A patient in their early teens · a clinical photograph of a skin lesion: 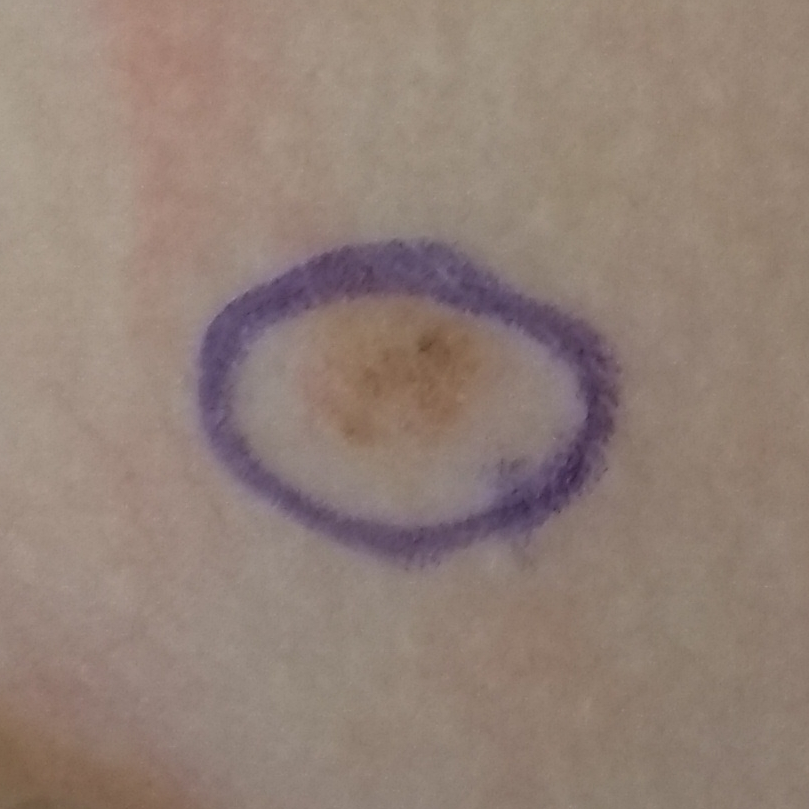Located on the neck. The patient describes that the lesion has grown. The consensus clinical diagnosis was a nevus.